A dermoscopic photograph of a skin lesion:
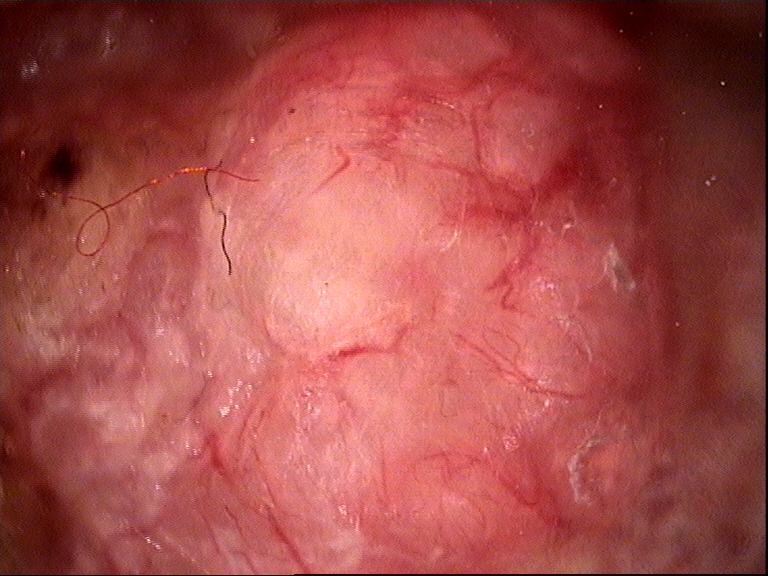Findings: The architecture is that of a keratinocytic lesion. Pathology: Biopsy-confirmed as a basal cell carcinoma.